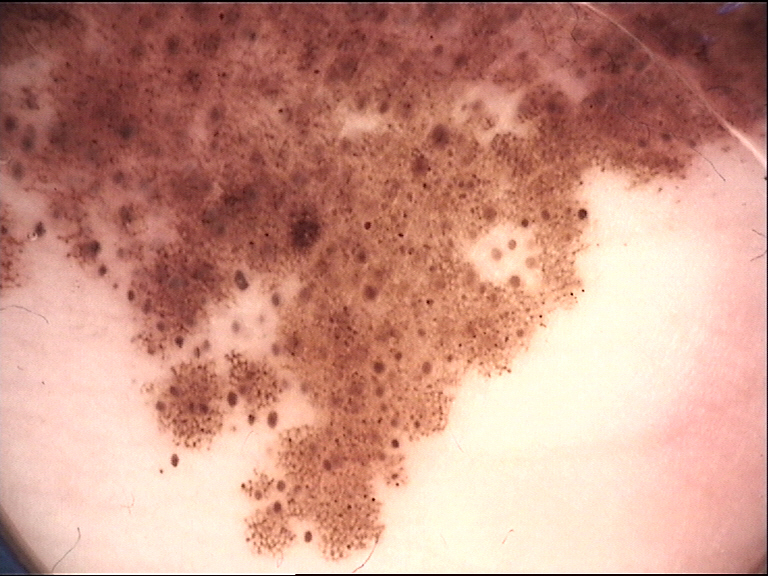class = congenital compound nevus (expert consensus).